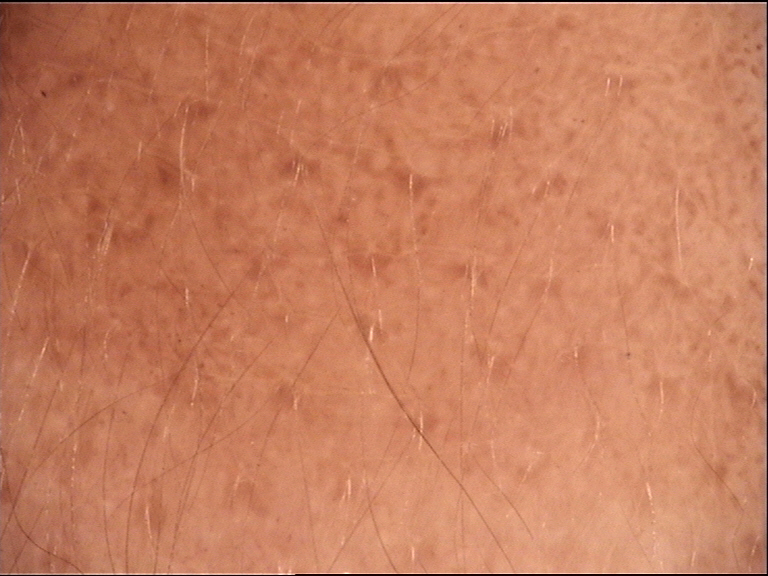modality = dermatoscopy, lesion type = banal, diagnosis = congenital junctional nevus (expert consensus).